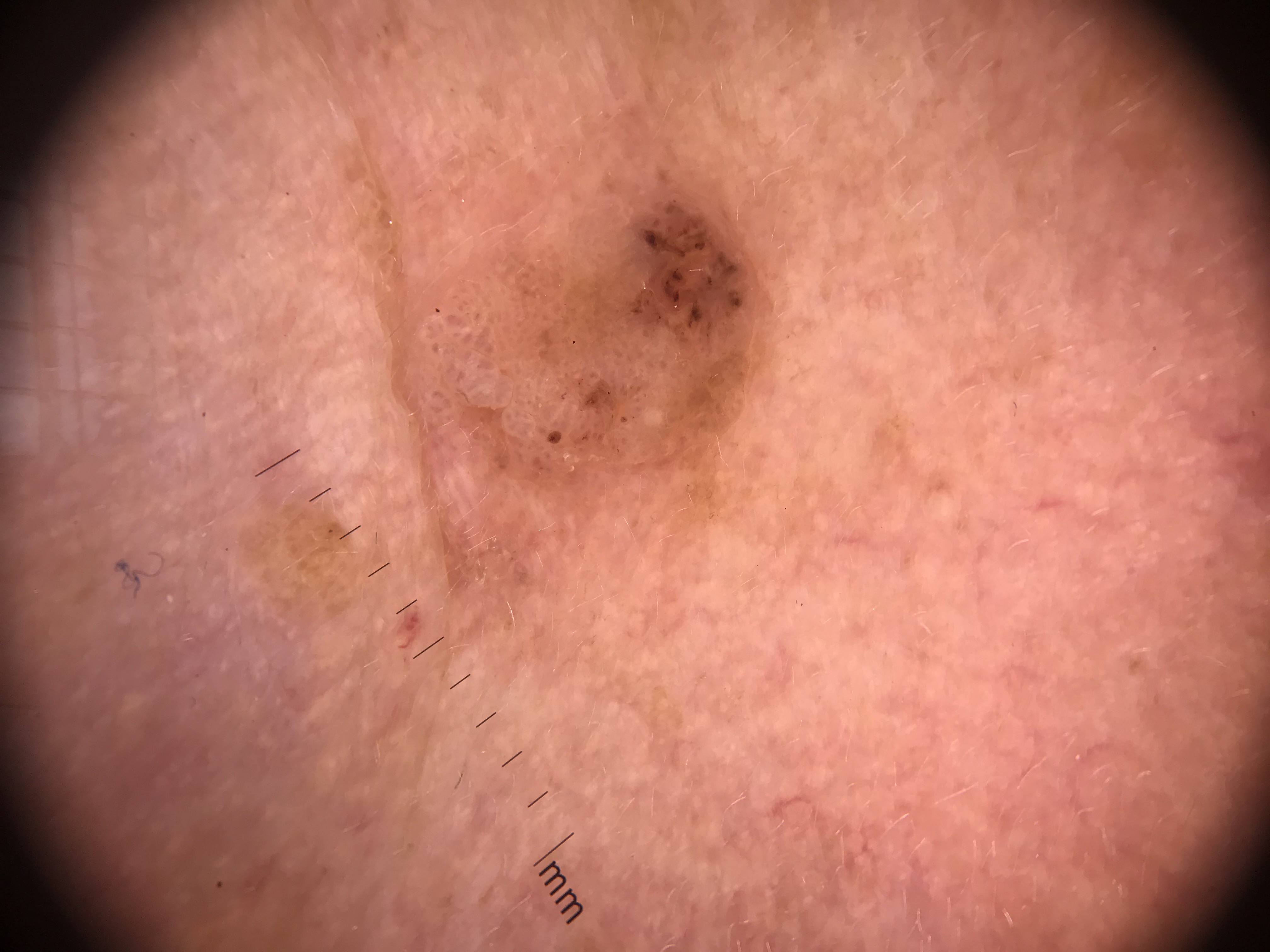<lesion>
<image>dermoscopy</image>
<diagnosis>
<name>seborrheic keratosis</name>
<code>sk</code>
<malignancy>benign</malignancy>
<super_class>non-melanocytic</super_class>
<confirmation>expert consensus</confirmation>
</diagnosis>
</lesion>